Dermoscopy of a skin lesion: 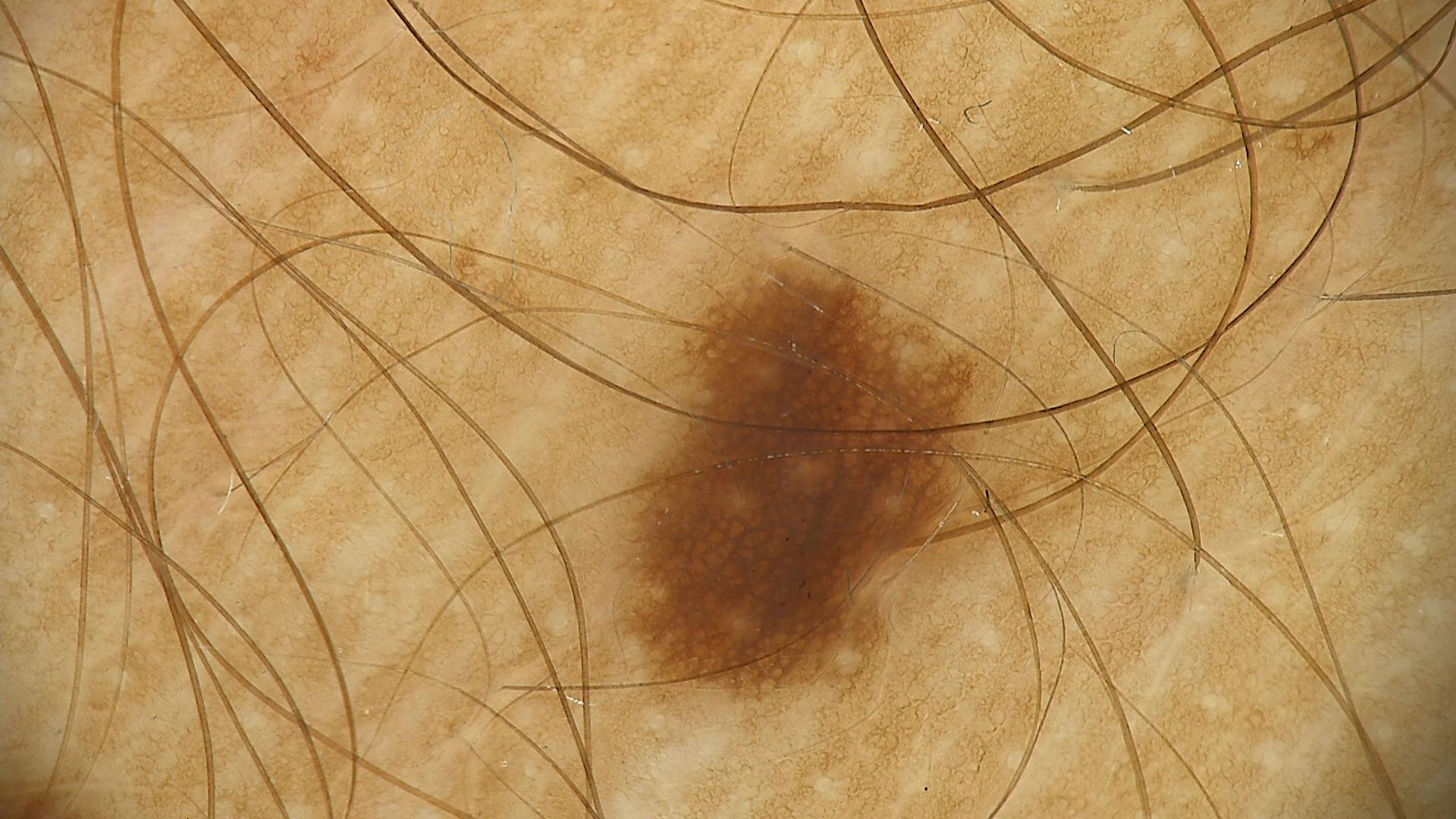The diagnosis was a benign lesion — a dysplastic junctional nevus.